The patient says their skin tans without first burning; a female patient 78 years old; a dermatoscopic image of a skin lesion; collected as part of a research study, without a referral diagnosis: 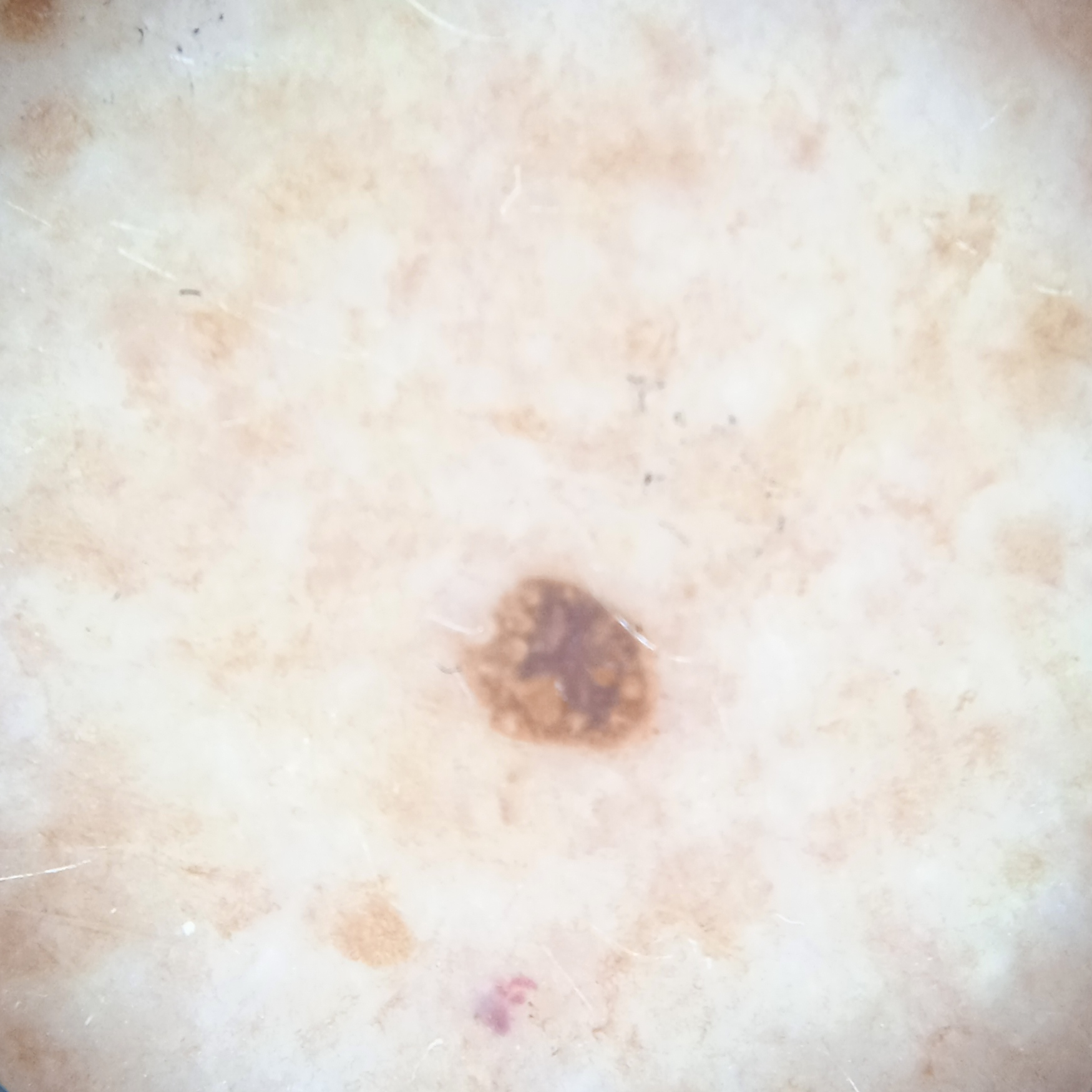The lesion is on an arm. Measuring roughly 2.4 mm. The dermatologists' assessment was a seborrheic keratosis.